An image taken at an angle · the patient is female · located on the arm: 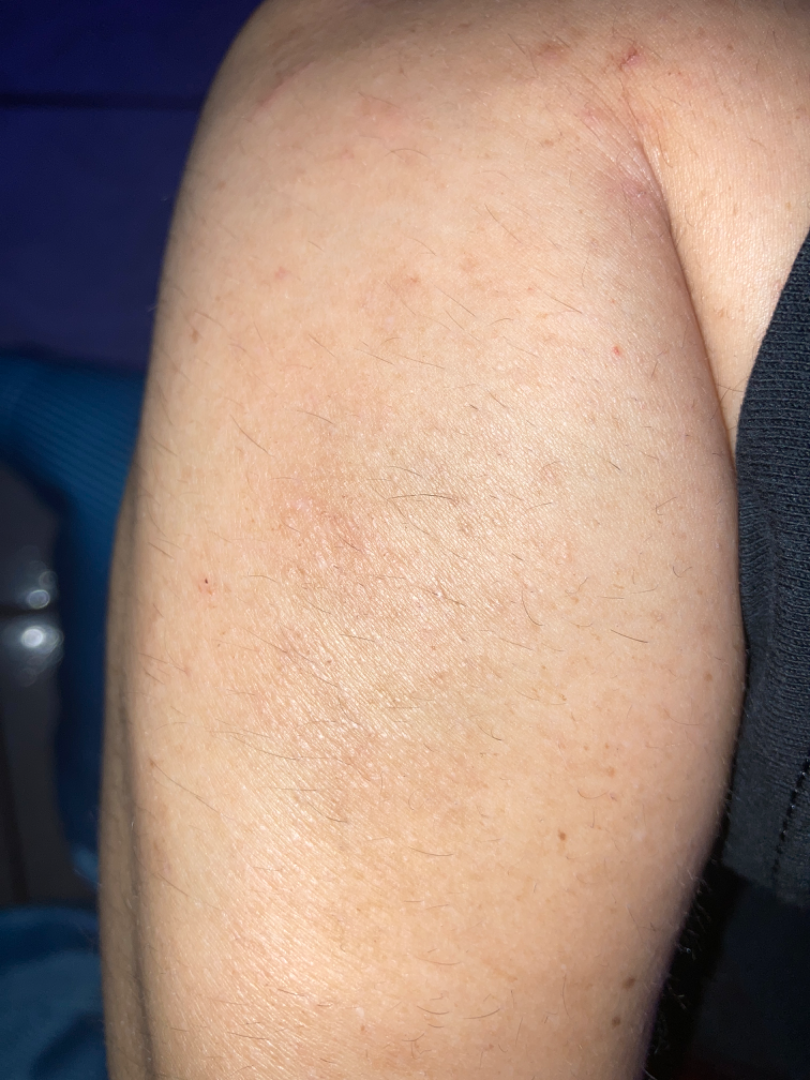History:
The lesion is described as rough or flaky. Fitzpatrick III; human graders estimated a Monk Skin Tone of 3.
Impression:
Reviewed remotely by three dermatologists: the reviewer's impression was Eczema.